A male patient in their 60s; a smartphone photograph of a skin lesion: 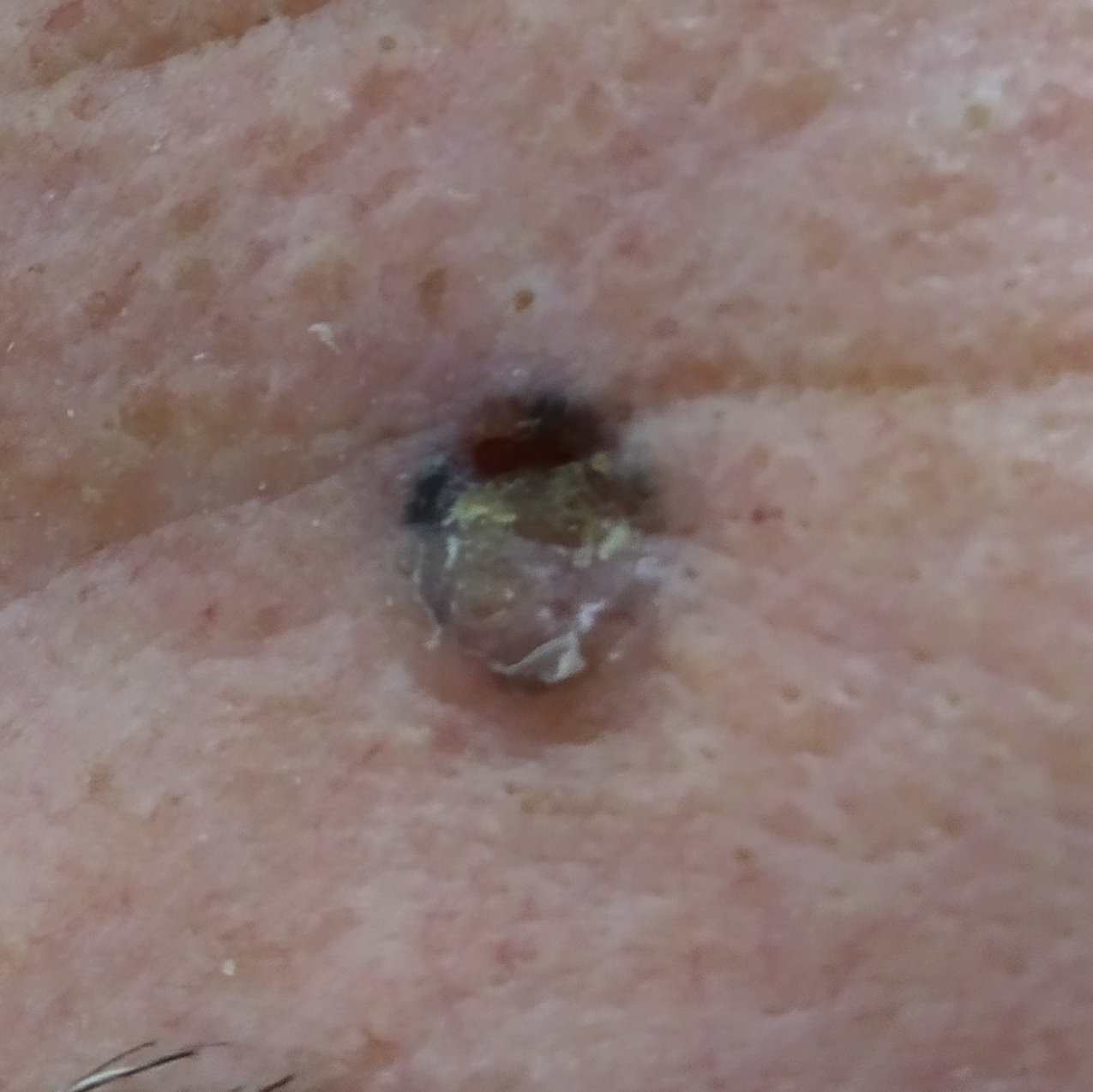anatomic site: the face; reported symptoms: itching, elevation, bleeding; pathology: basal cell carcinoma (biopsy-proven).